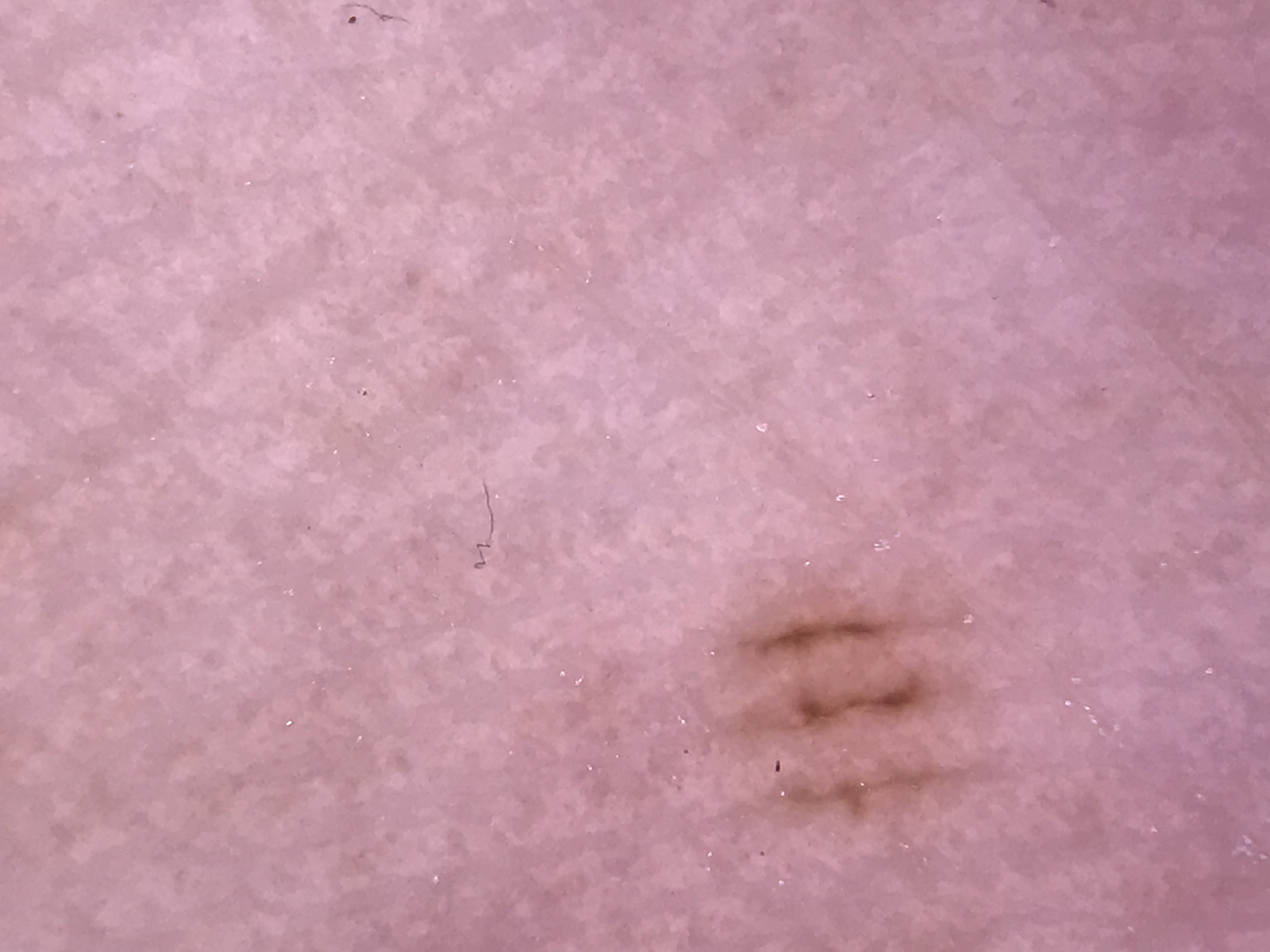diagnosis = acral junctional nevus (expert consensus).